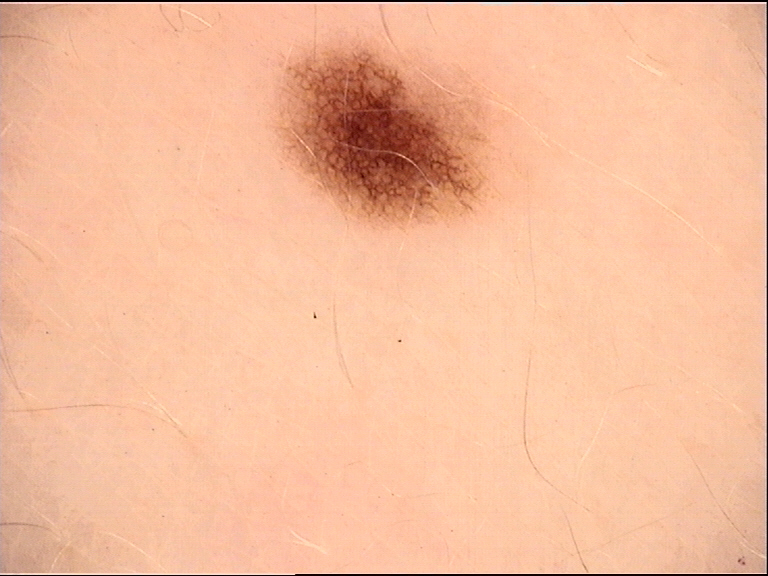Labeled as a junctional nevus.